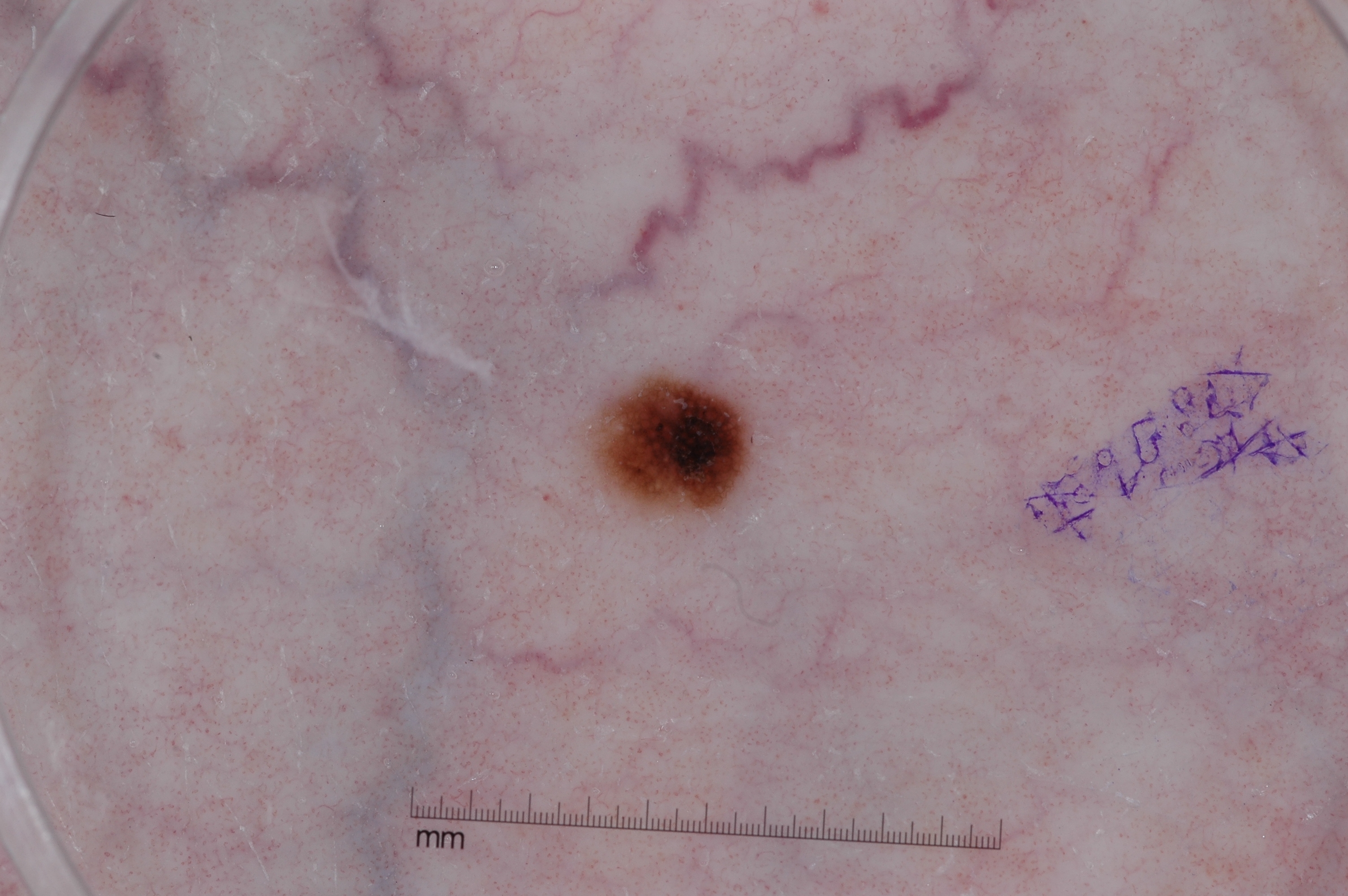Case summary: A skin lesion imaged with a dermatoscope. A female patient, approximately 60 years of age. In (x1, y1, x2, y2) order, the lesion is bounded by 590/378/758/518. Dermoscopic assessment notes pigment network. Conclusion: The lesion was assessed as a melanocytic nevus.